A dermoscopy image of a single skin lesion:
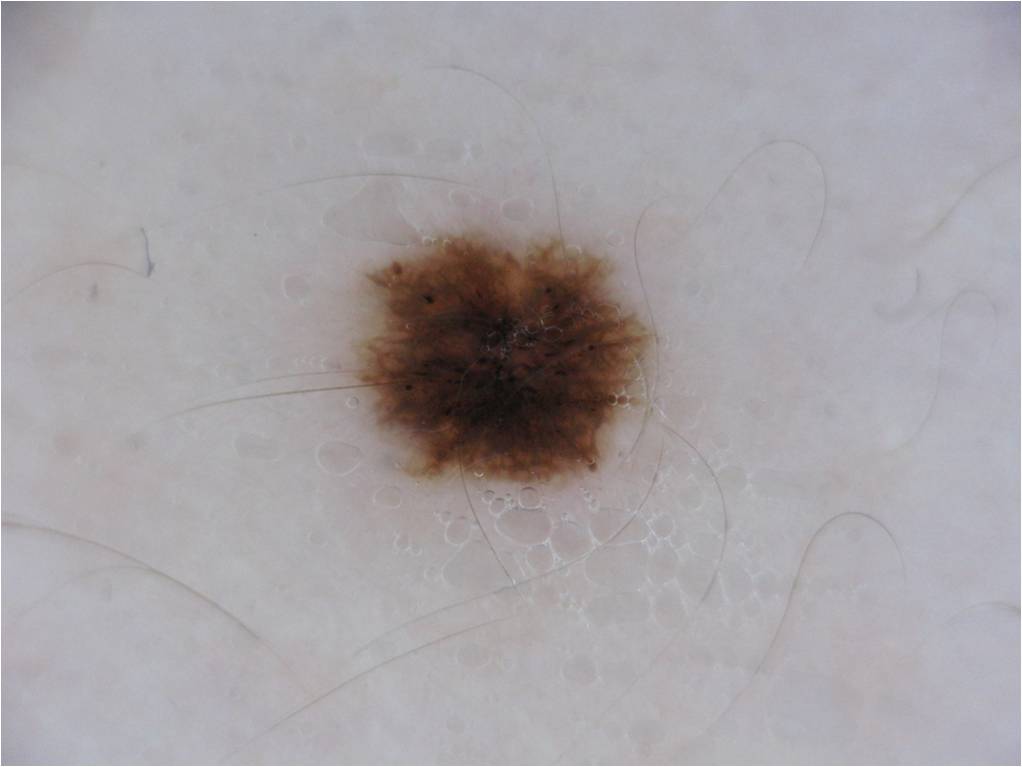On dermoscopy, the lesion shows pigment network, globules, and streaks, with no milia-like cysts or negative network. With coordinates (x1, y1, x2, y2), the lesion spans [362,231,646,480]. Clinically diagnosed as a melanocytic nevus, a benign skin lesion.